Female patient, age 18–29; the leg is involved; the photo was captured at a distance; the lesion is associated with itching; the patient considered this a rash; present for one to four weeks:
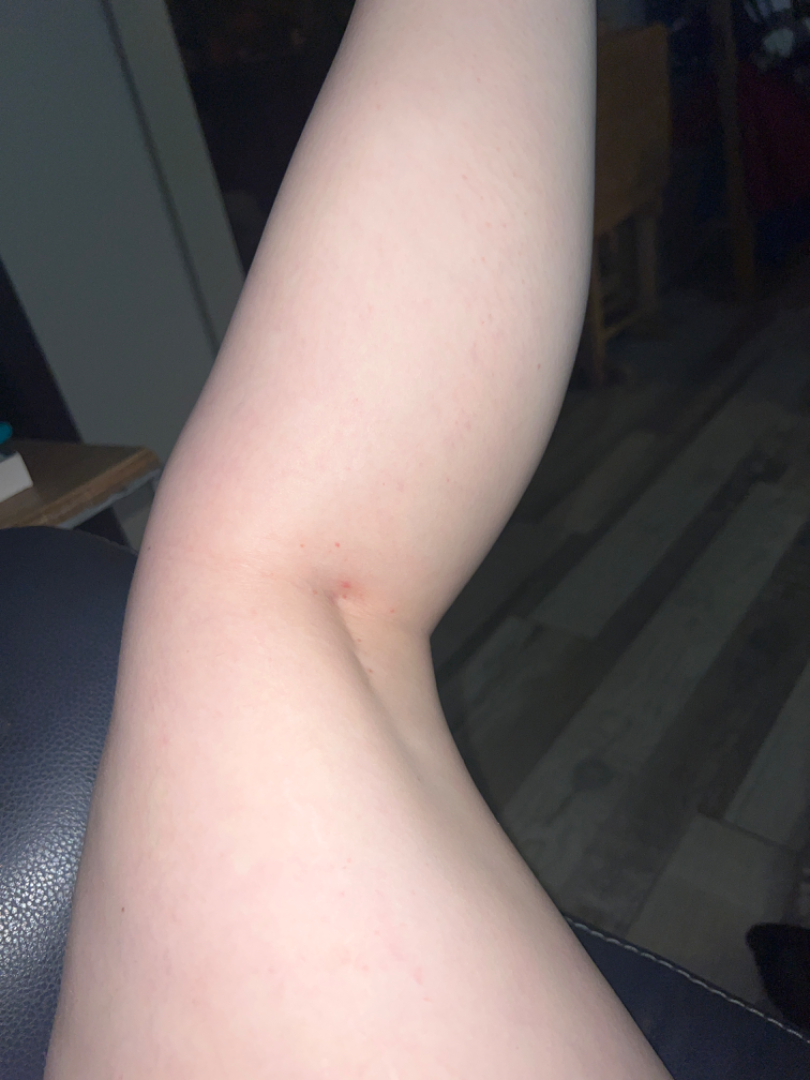Three independent reviewers: favoring Miliaria; also raised was Folliculitis; an alternative is Molluscum Contagiosum; a remote consideration is Irritant Contact Dermatitis.